The subject is a male aged 30–39; the front of the torso and back of the torso are involved; a close-up photograph: 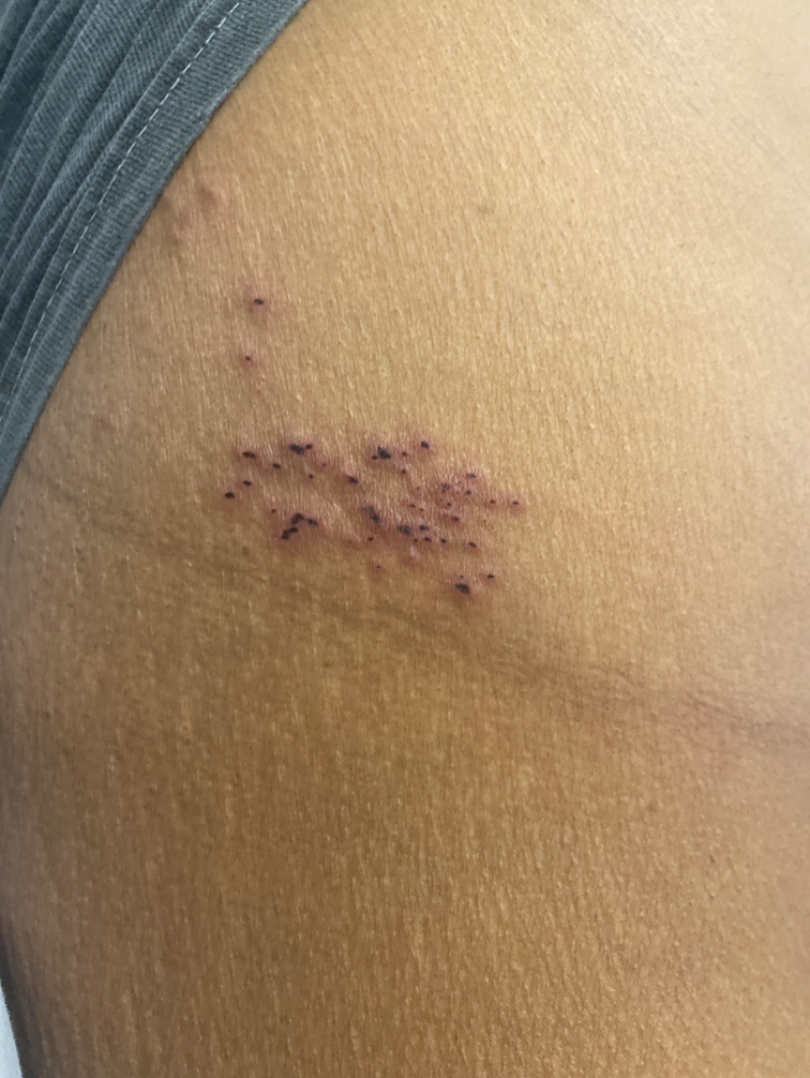The patient reports the condition has been present for one to four weeks. The patient reports the lesion is raised or bumpy. The patient considered this a rash. Herpes Simplex (0.41); Herpes Zoster (0.31); Lymphangioma (0.21); Dermatitis herpetiformis (0.07).